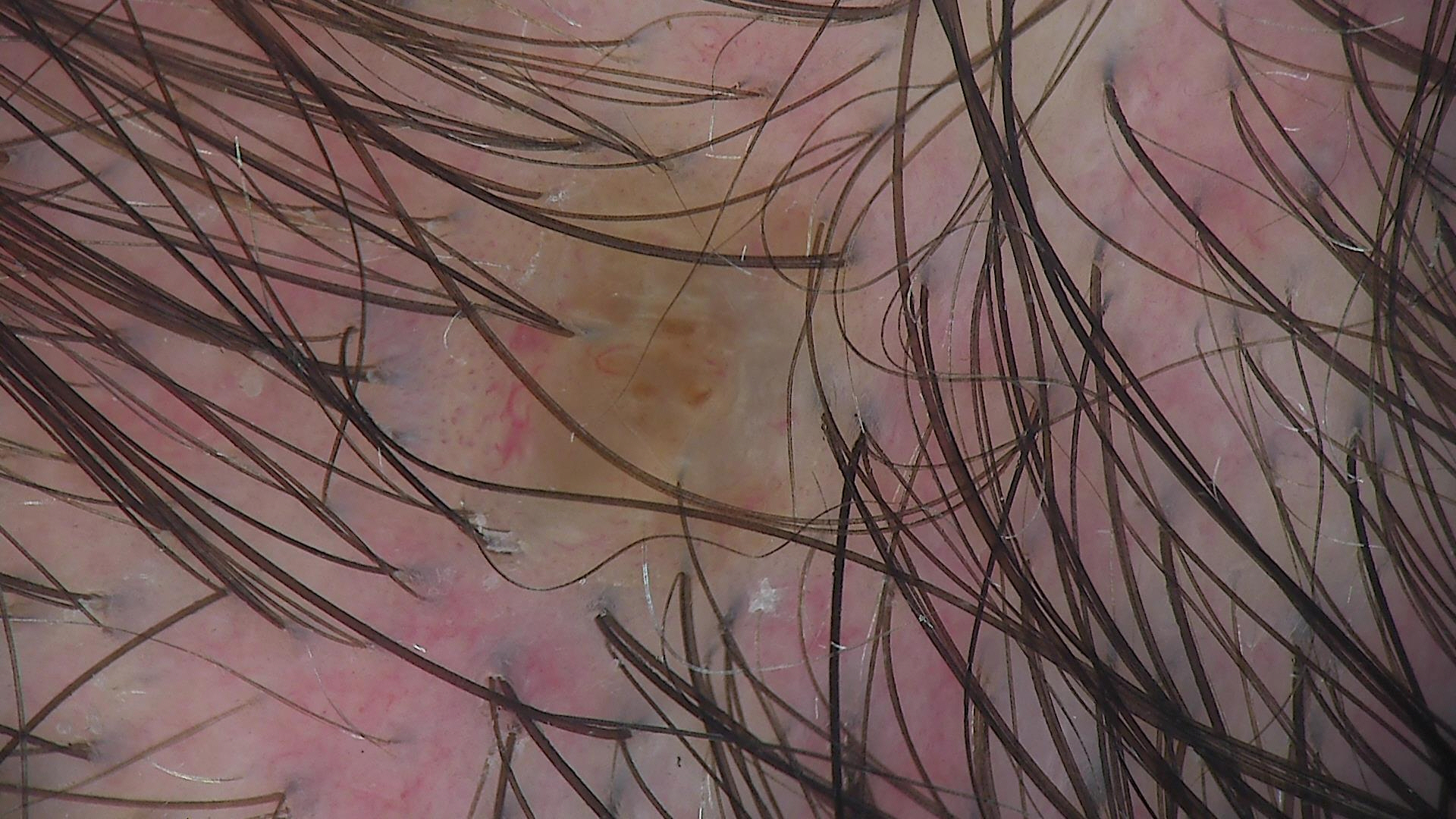This is a banal lesion. Diagnosed as a dermal nevus.